The photo was captured at a distance · the affected area is the arm · the patient is a male aged 40–49.
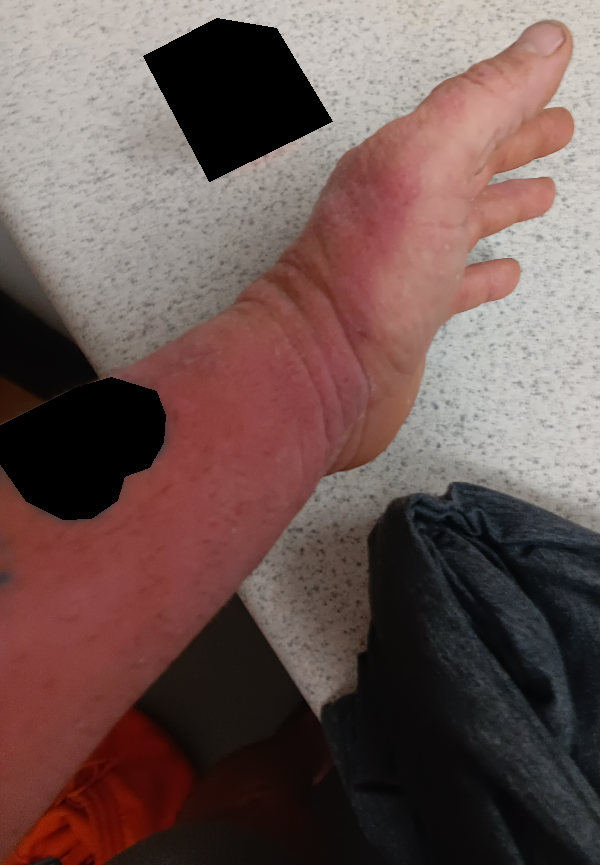* differential — most likely Cutaneous lupus